A dermoscopic photograph of a skin lesion:
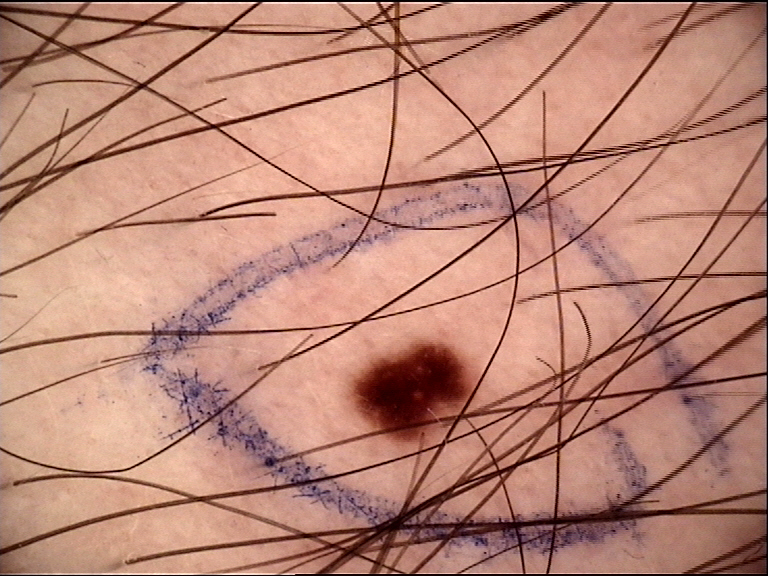Conclusion:
Consistent with a benign lesion — a dysplastic junctional nevus.